The patient is Fitzpatrick skin type III. Per the chart, a first-degree relative with melanoma. A male subject roughly 40 years of age. Contact-polarized dermoscopy of a skin lesion — 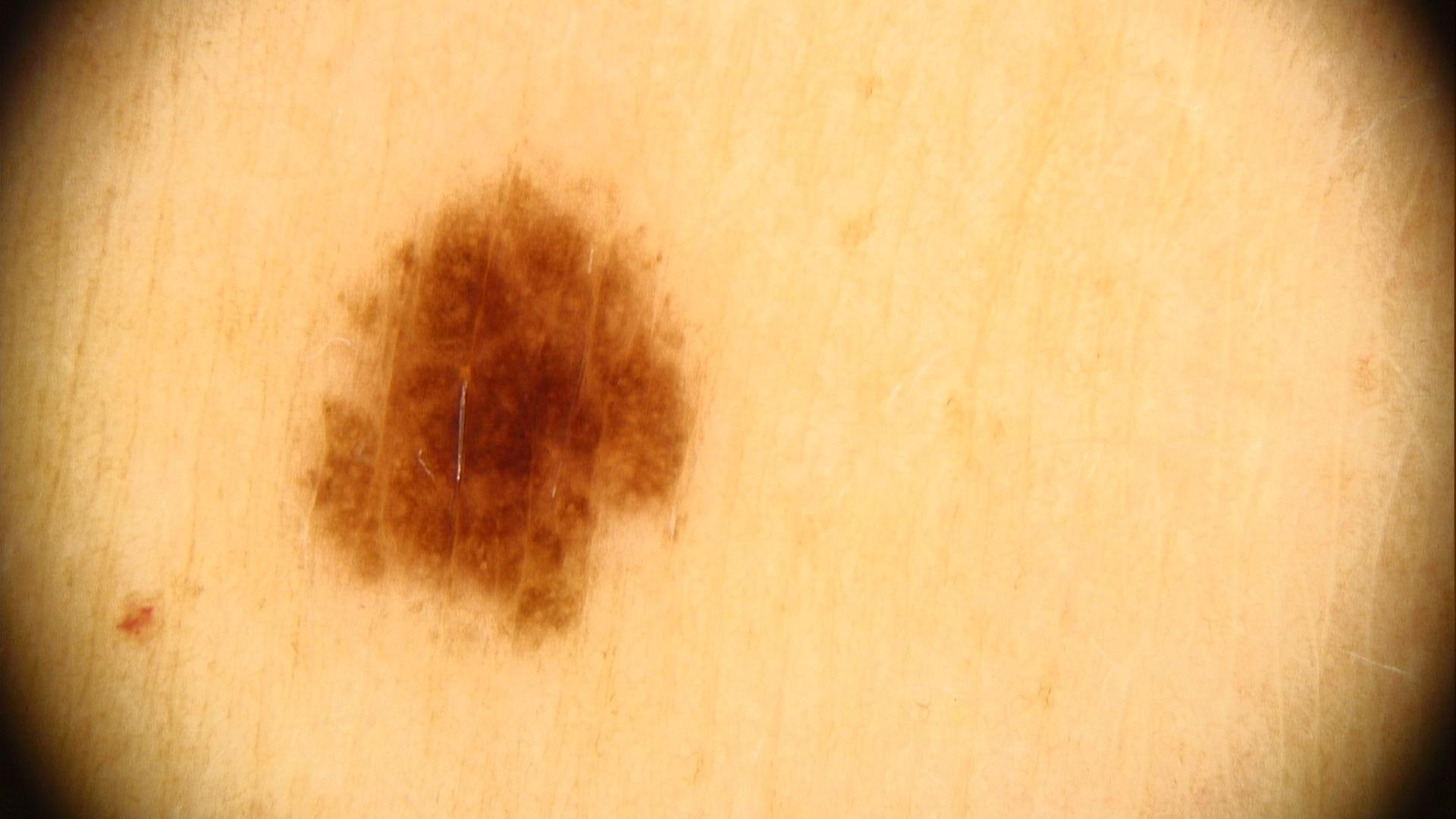Q: Where on the body is the lesion?
A: the posterior trunk
Q: What is the diagnosis?
A: Nevus